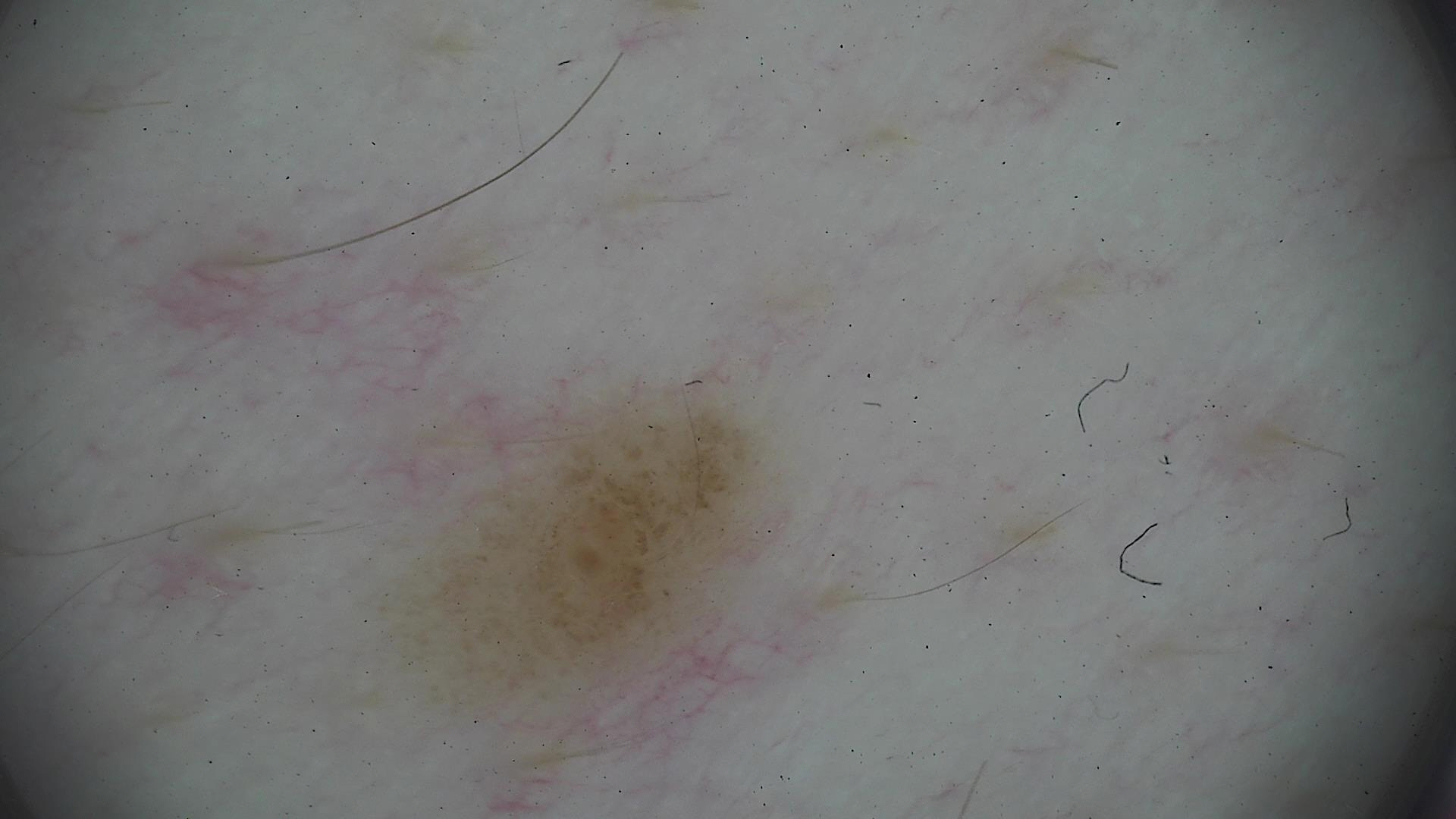A dermoscopic photograph of a skin lesion. Diagnosed as a benign lesion — a dysplastic junctional nevus.